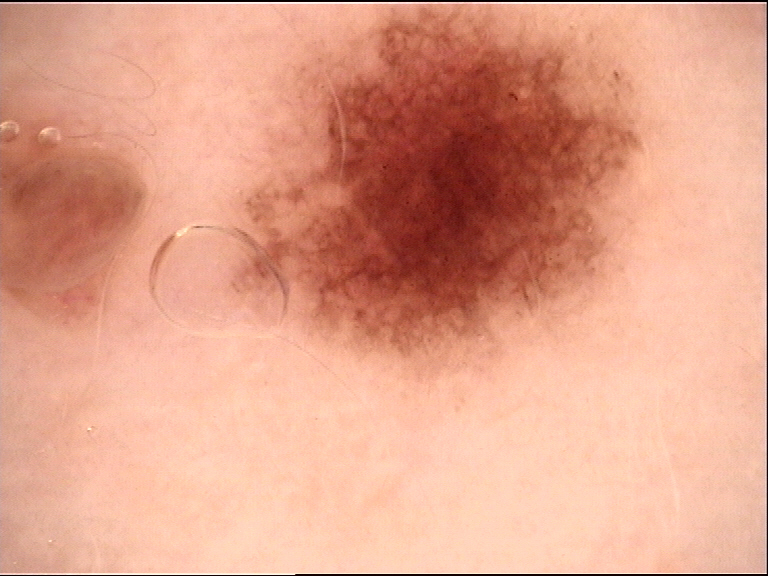image = dermatoscopy; assessment = dysplastic junctional nevus (expert consensus).